This is a close-up image · the affected area is the arm — 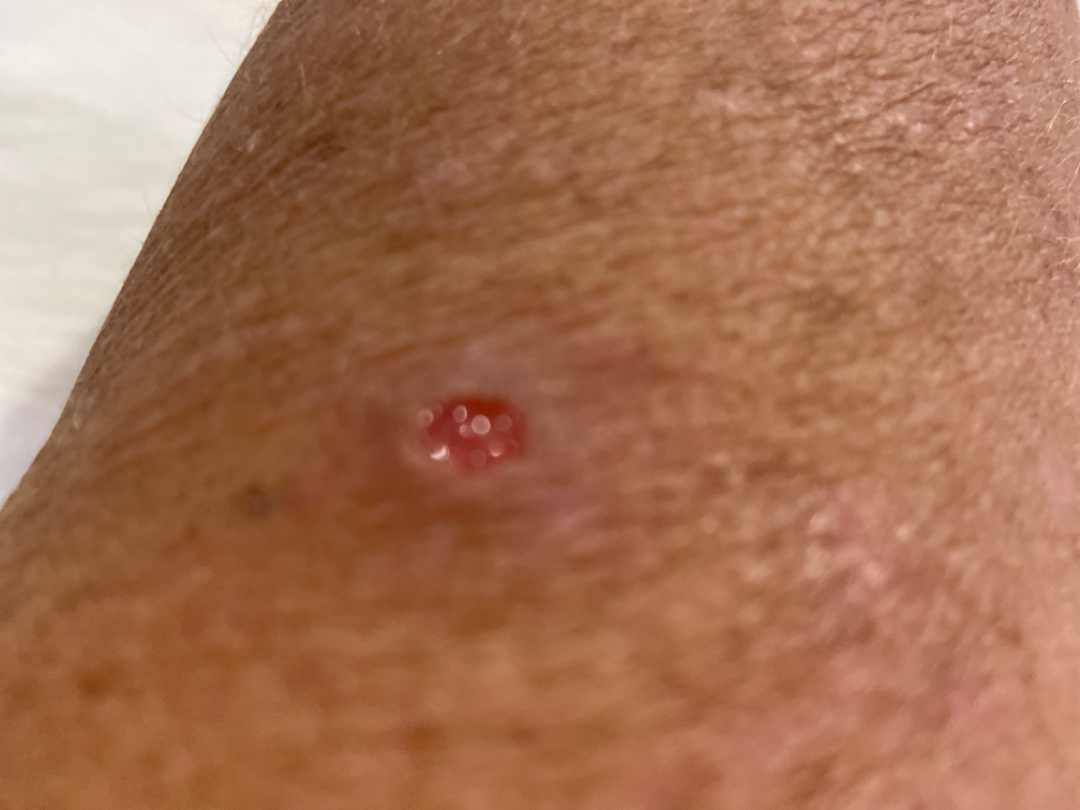The dermatologist could not determine a likely condition from the photograph alone. No constitutional symptoms were reported. The lesion is described as rough or flaky and fluid-filled. Skin tone: Fitzpatrick skin type IV. The lesion is associated with bothersome appearance.